A dermoscopic image of a skin lesion.
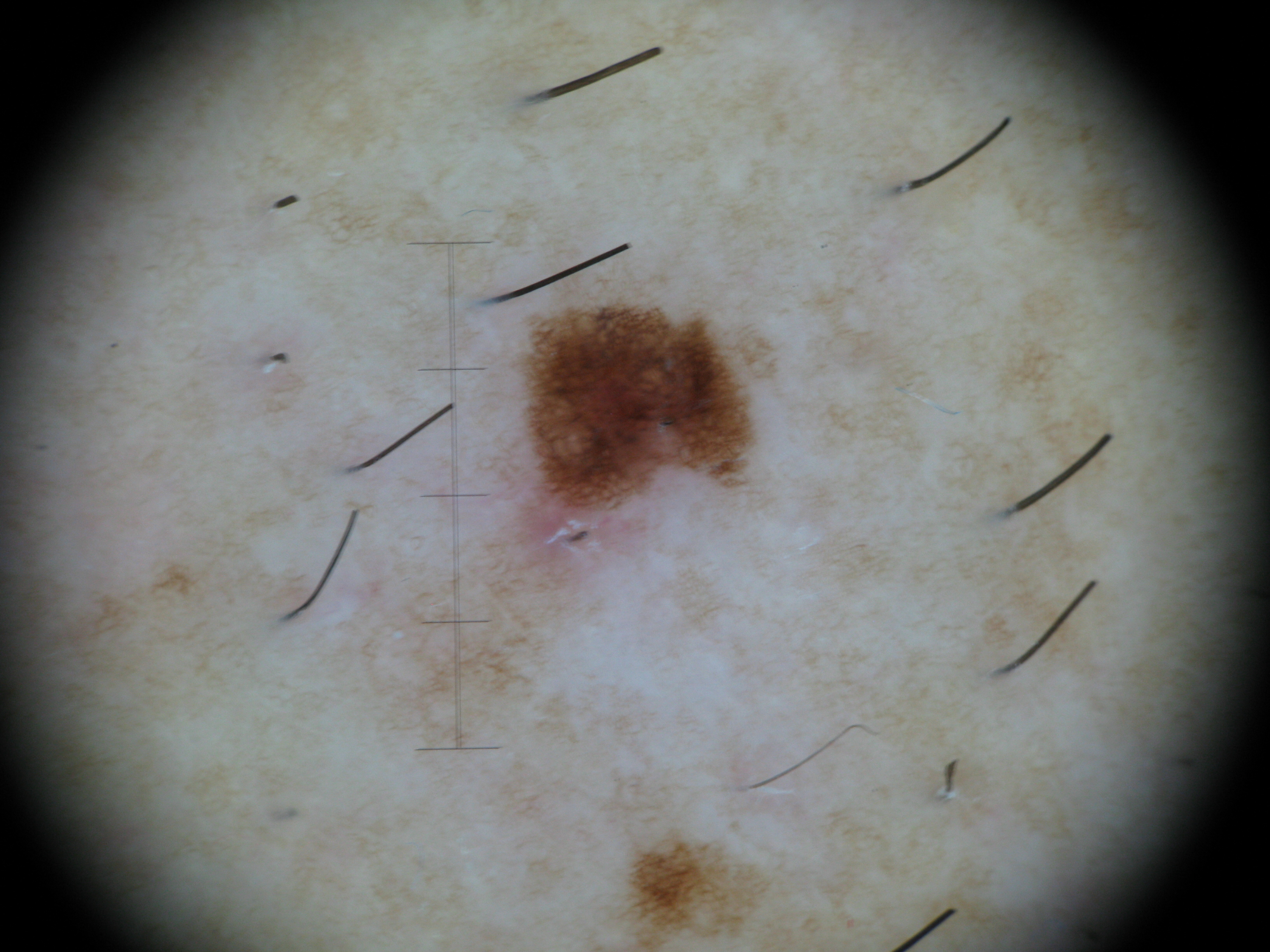Diagnosed as a benign lesion — a dysplastic junctional nevus.